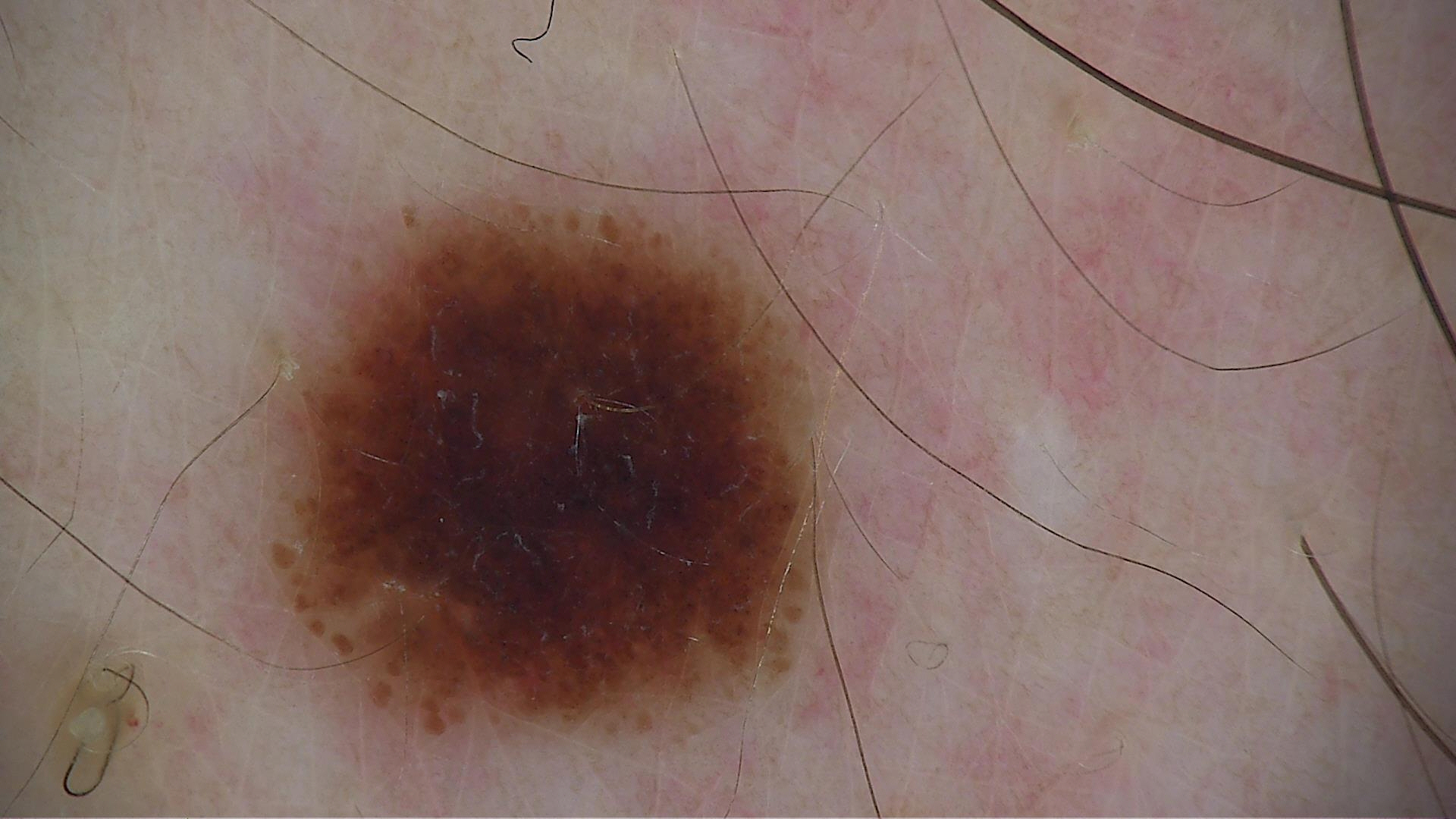Classified as a benign lesion — a dysplastic junctional nevus.